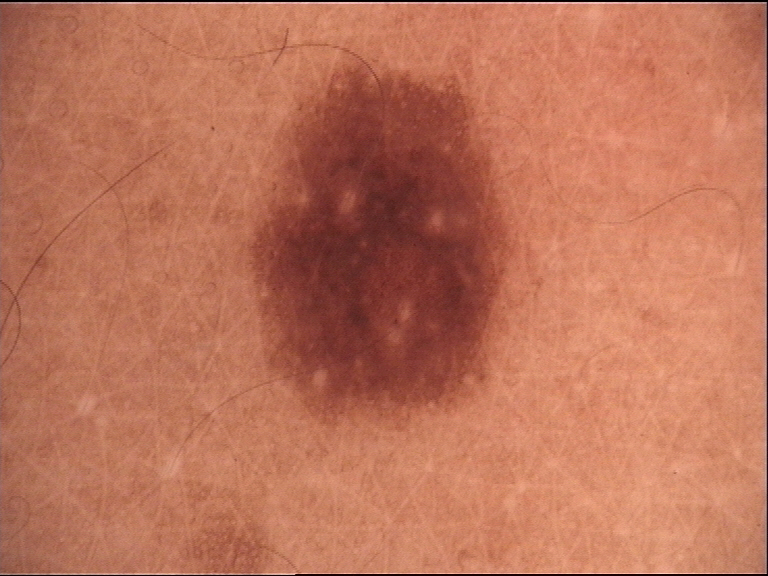<dermoscopy>
  <image>dermatoscopy</image>
  <diagnosis>
    <name>junctional nevus</name>
    <code>jb</code>
    <malignancy>benign</malignancy>
    <super_class>melanocytic</super_class>
    <confirmation>expert consensus</confirmation>
  </diagnosis>
</dermoscopy>